A dermoscopic photograph of a skin lesion.
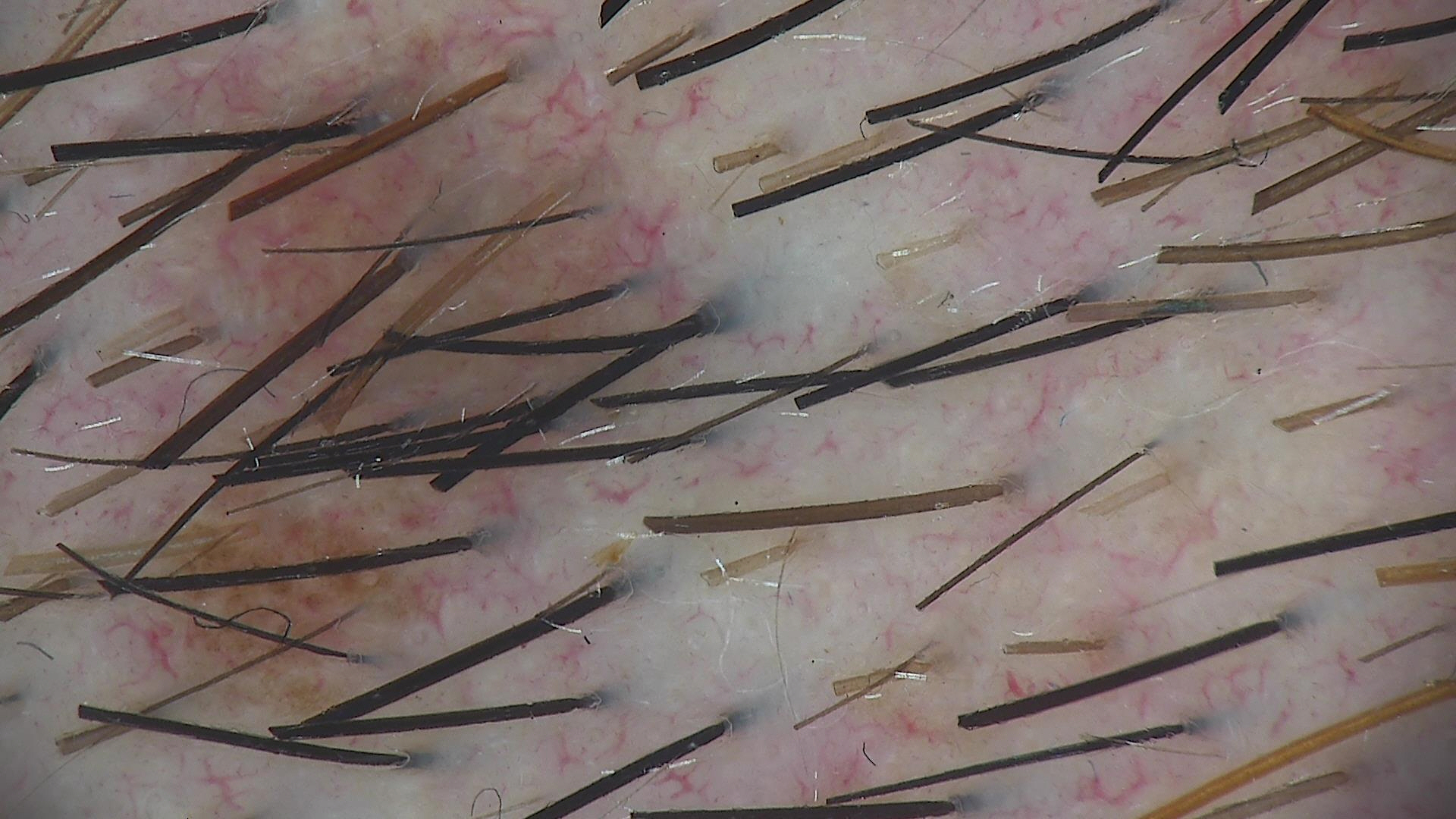diagnosis: dysplastic junctional nevus (expert consensus).